A skin lesion imaged with a dermatoscope:
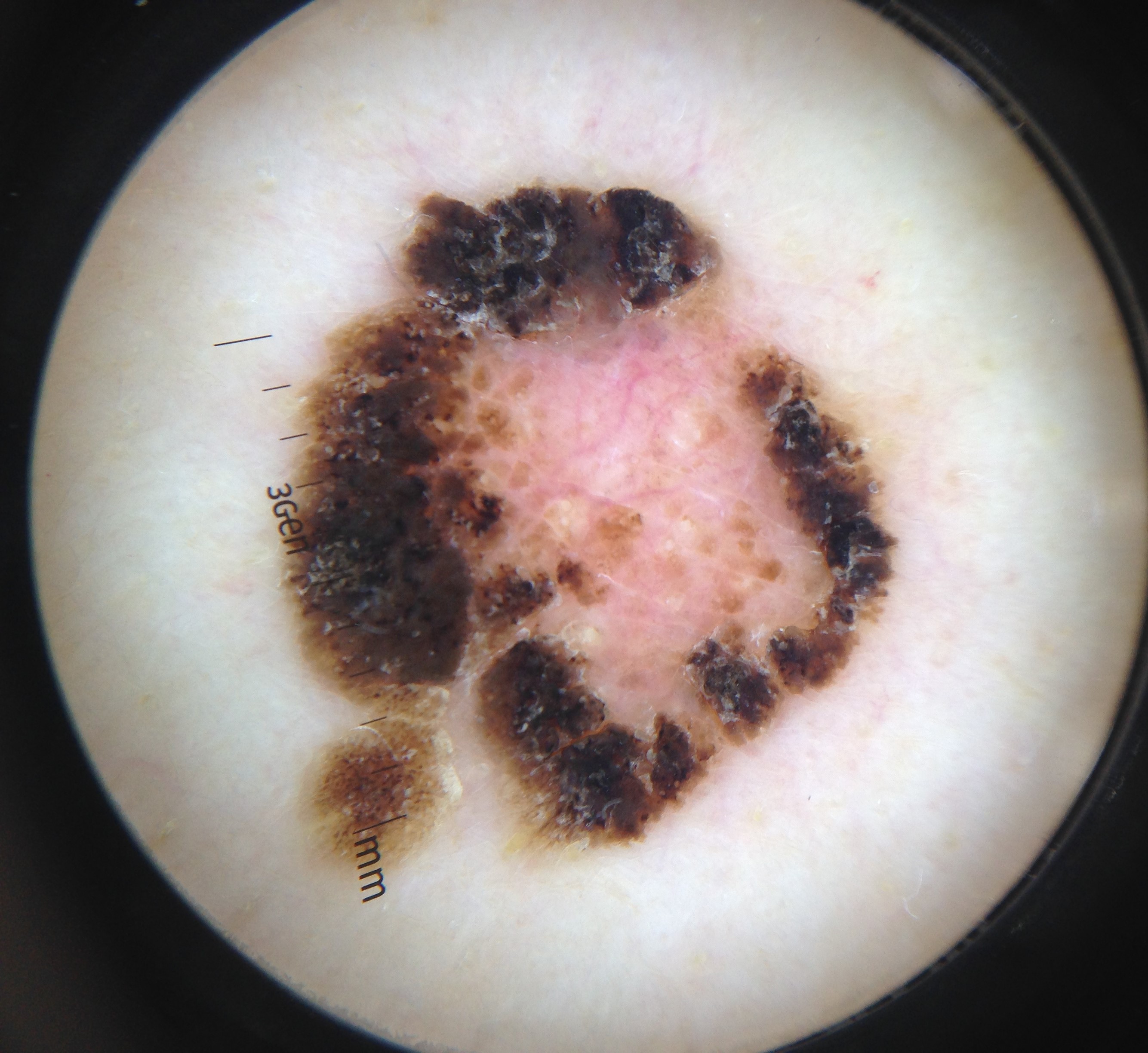Impression: The diagnostic label was a benign lesion — a seborrheic keratosis.